A dermoscopic image of a skin lesion — 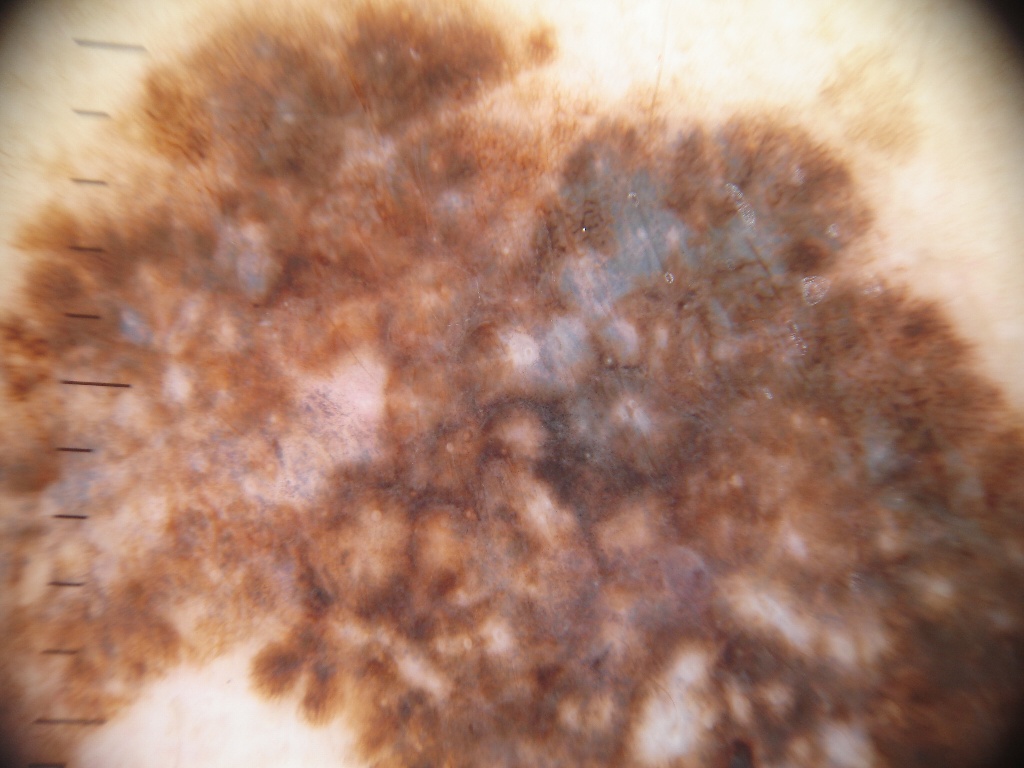lesion_location: spans the dermoscopic field
dermoscopic_features:
  present:
    - pigment network
  absent:
    - streaks
    - globules
    - negative network
    - milia-like cysts
diagnosis:
  name: melanoma
  malignancy: malignant
  lineage: melanocytic
  provenance: histopathology